A skin lesion imaged with a dermatoscope — 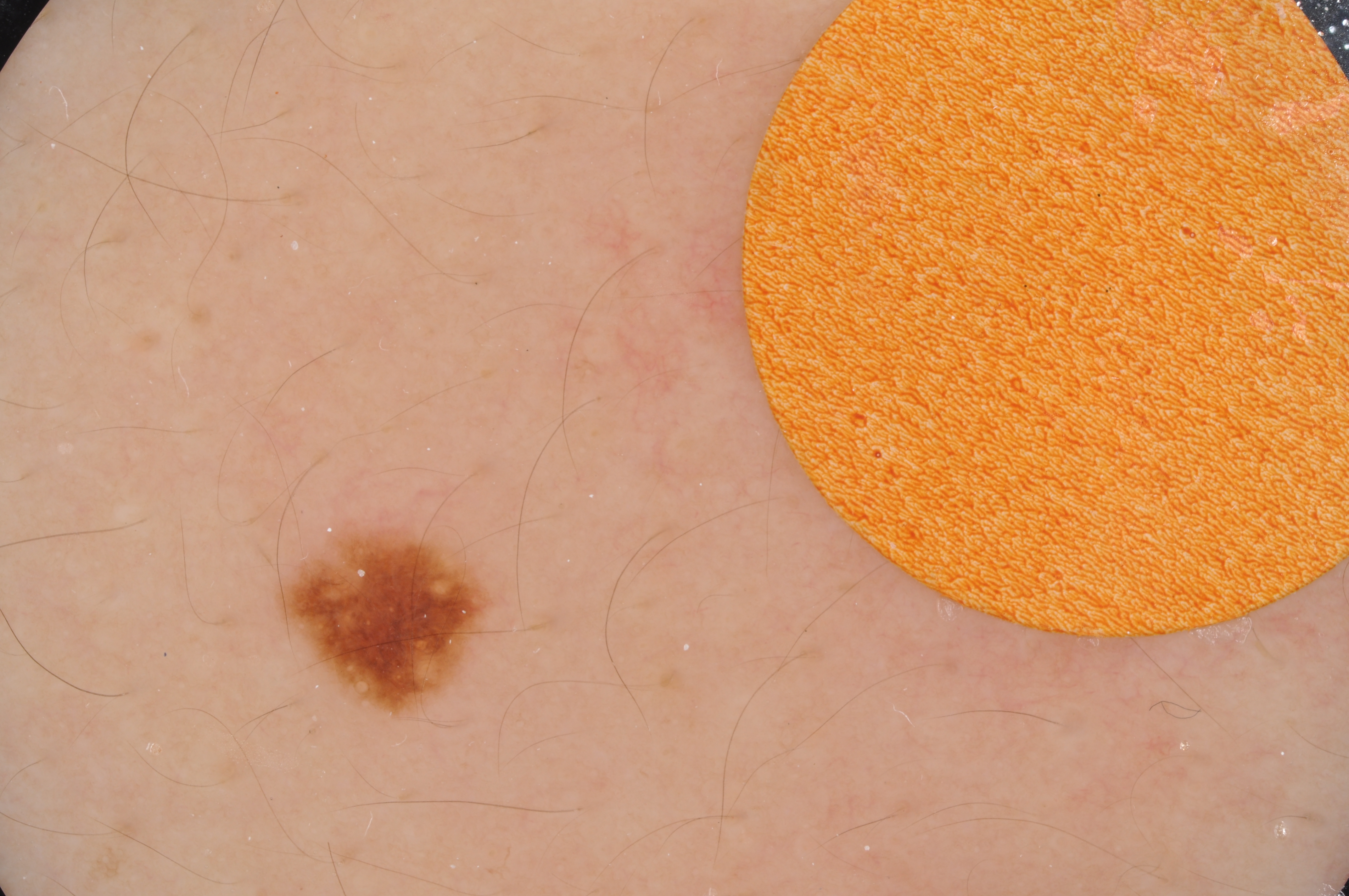lesion bbox = 269/525/506/722
extent = small
assessment = a benign skin lesion